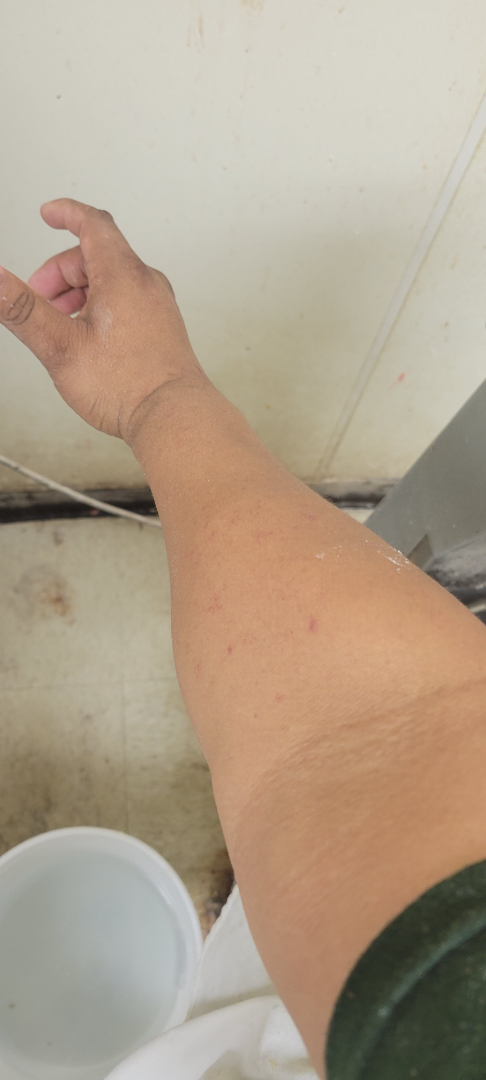| field | value |
|---|---|
| systemic symptoms | none reported |
| lesion symptoms | none reported |
| anatomic site | arm |
| history | one to three months |
| skin tone | FST V; human graders estimated Monk skin tone scale 3 or 4 (two reviewer pools) |
| self-categorized as | a rash |
| shot type | at a distance |
| clinical impression | the differential is split between Pigmented purpuric eruption and Leukocytoclastic Vasculitis |